The patient considered this a pigmentary problem; this image was taken at an angle; no constitutional symptoms were reported; located on the front of the torso; texture is reported as flat; the contributor is 18–29, male; the contributor reports the condition has been present for three to twelve months.
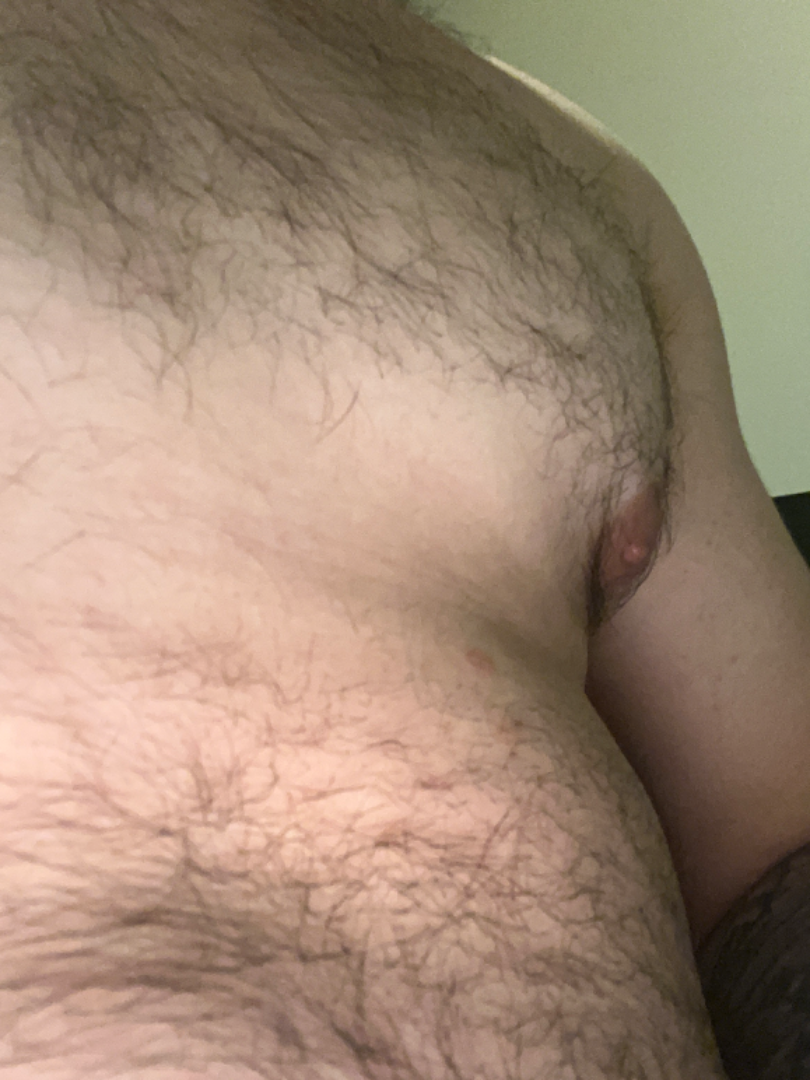The skin findings could not be characterized from the image.